The top or side of the foot is involved; a close-up photograph; female subject, age 30–39 — 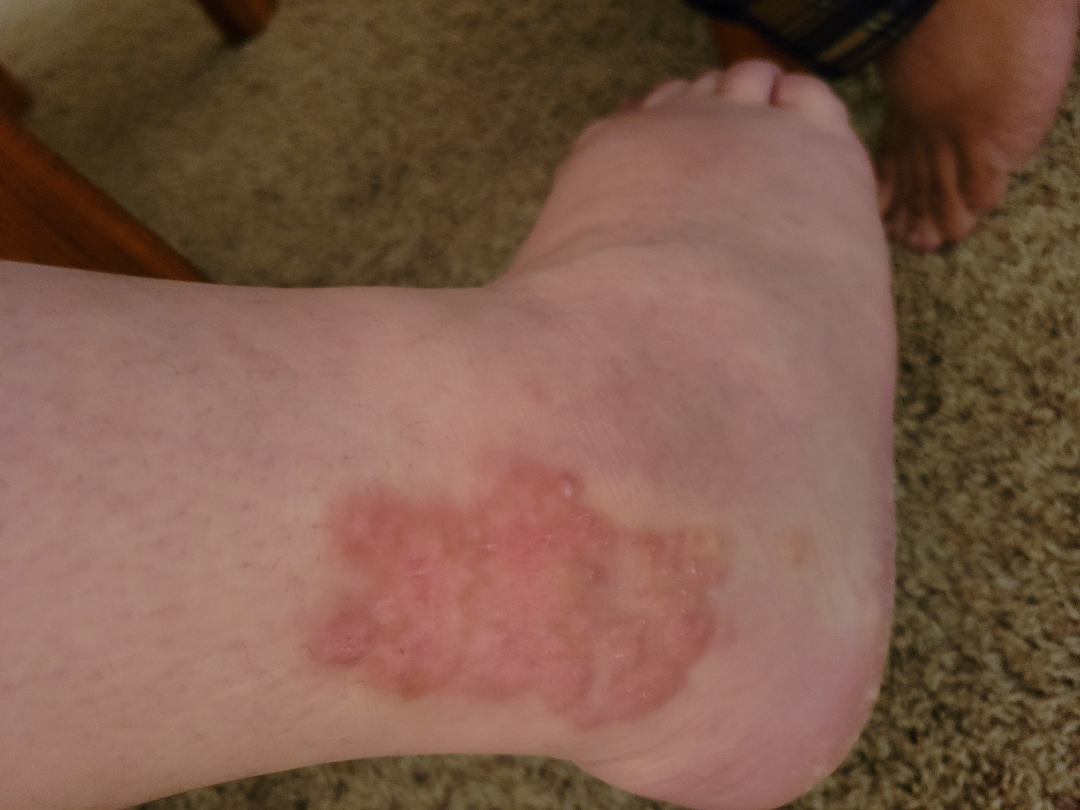onset = more than one year | lesion symptoms = enlargement, bothersome appearance, burning and itching | surface texture = rough or flaky and raised or bumpy | patient's own categorization = a rash | diagnostic considerations = most likely Cutaneous T Cell Lymphoma; possibly Parapsoriasis; lower on the differential is deep fungal infection.